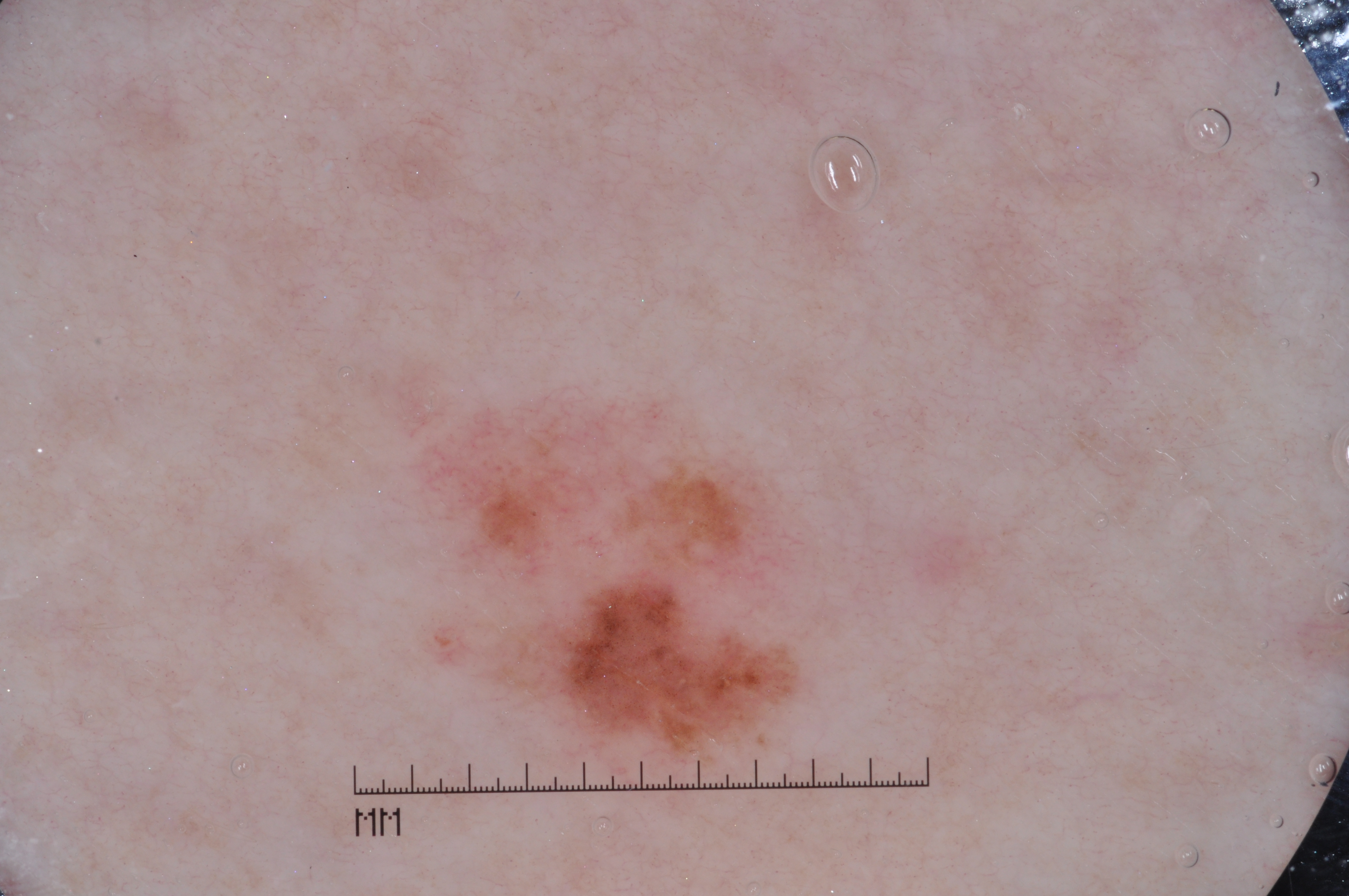  image:
    modality: dermoscopy
  patient:
    sex: female
    age_approx: 55
  dermoscopic_features:
    present:
      - milia-like cysts
    absent:
      - negative network
      - streaks
      - pigment network
  lesion_location:
    bbox_xyxy:
      - 443
      - 406
      - 801
      - 756
  lesion_extent:
    approx_field_fraction_pct: 7
  diagnosis:
    name: melanoma
    malignancy: malignant
    lineage: melanocytic
    provenance: histopathology